This is a close-up image · the lesion involves the arm · the contributor is a male aged 30–39 · texture is reported as flat · the patient reported no systemic symptoms · reported duration is about one day · no relevant lesion symptoms reported · the patient considered this a rash.
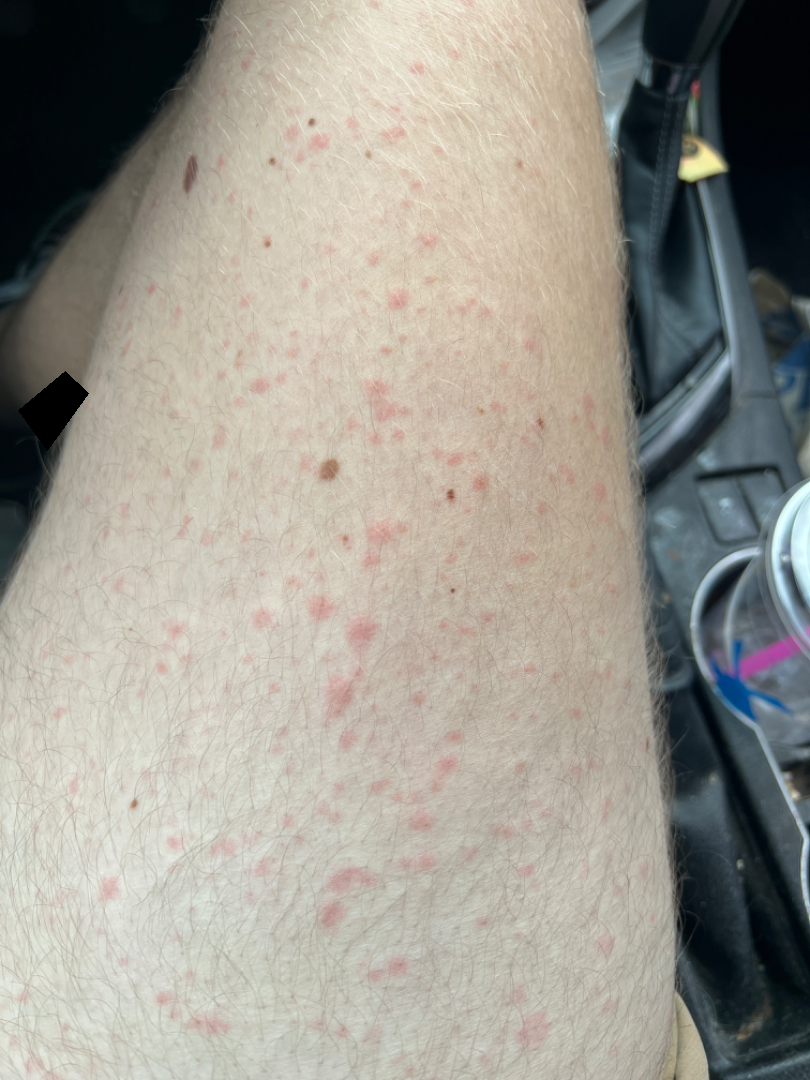On dermatologist assessment of the image: the favored diagnosis is Viral Exanthem.